The photograph is a close-up of the affected area; located on the back of the torso.
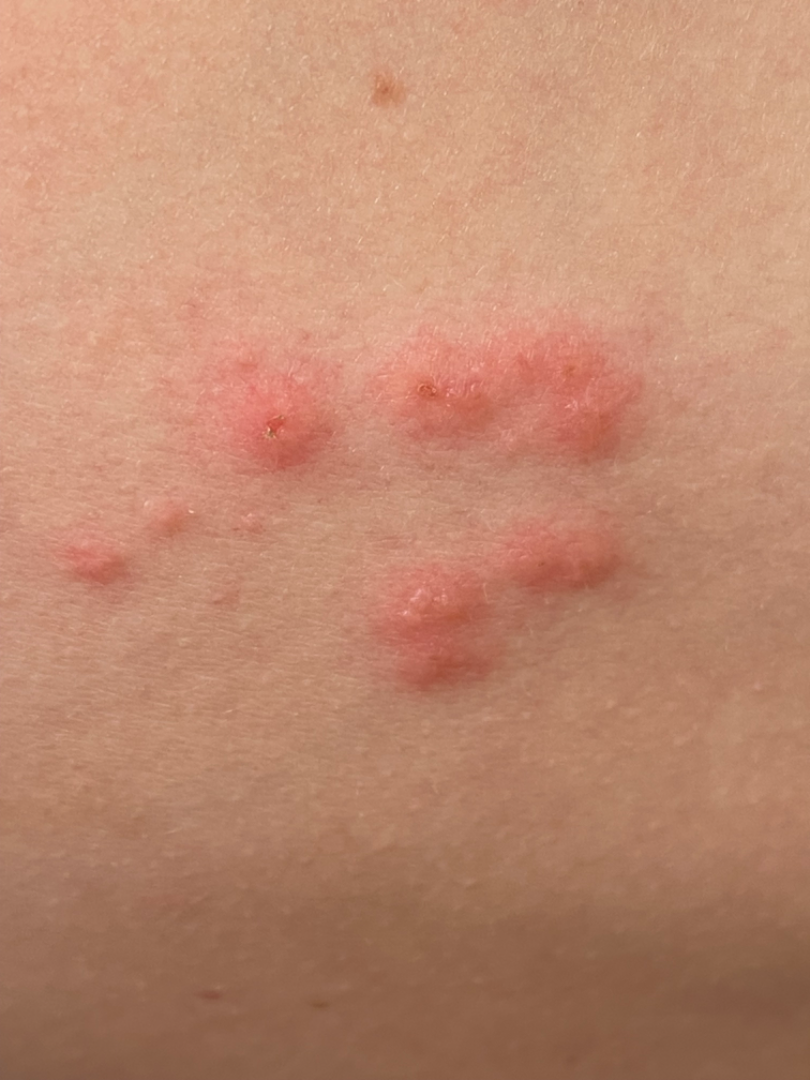<case>
  <differential>
    <leading>Herpes Zoster</leading>
  </differential>
</case>